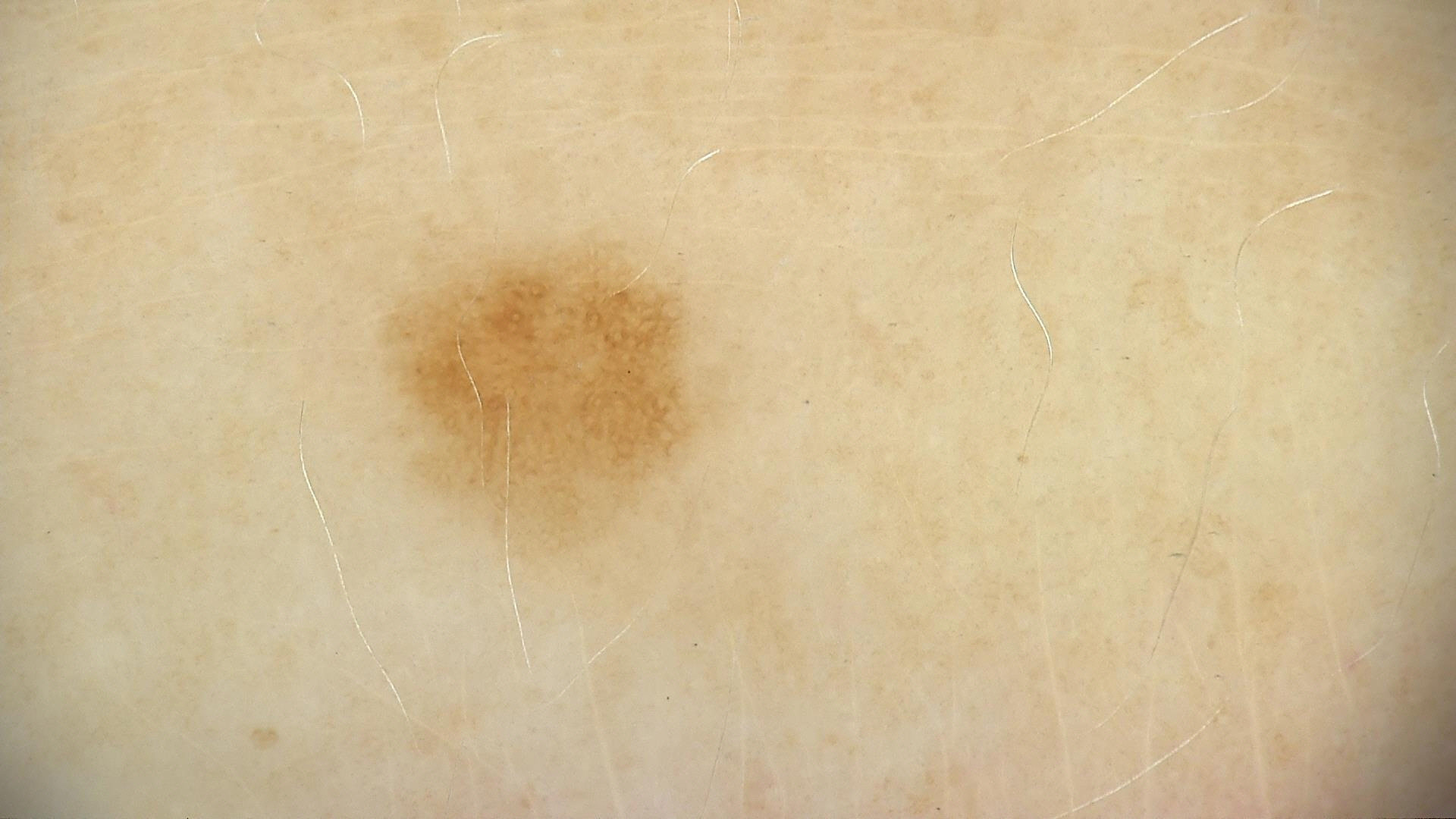A dermoscopy image of a single skin lesion. Labeled as a dysplastic junctional nevus.